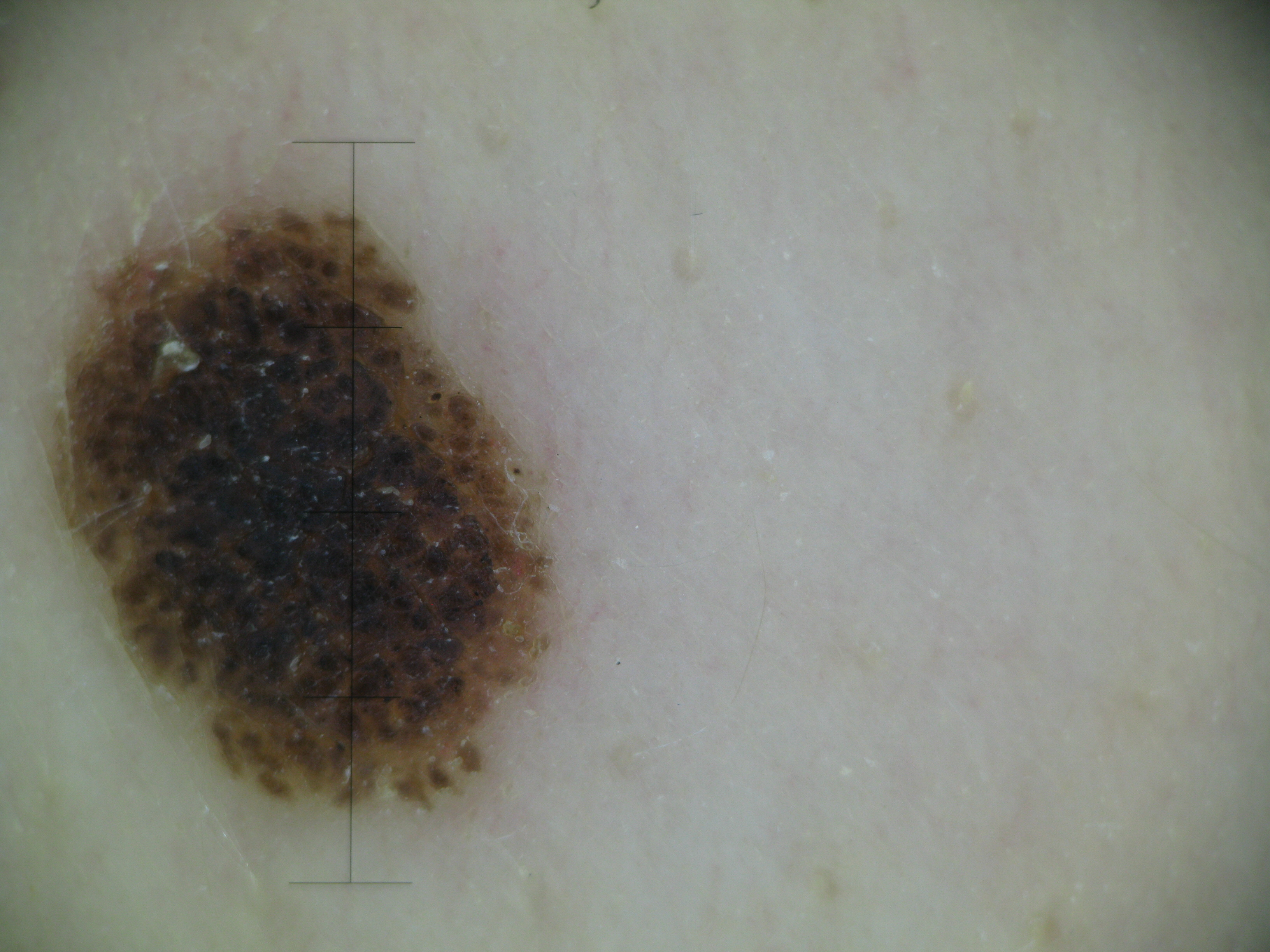This is a banal lesion.
The diagnosis was a compound nevus.